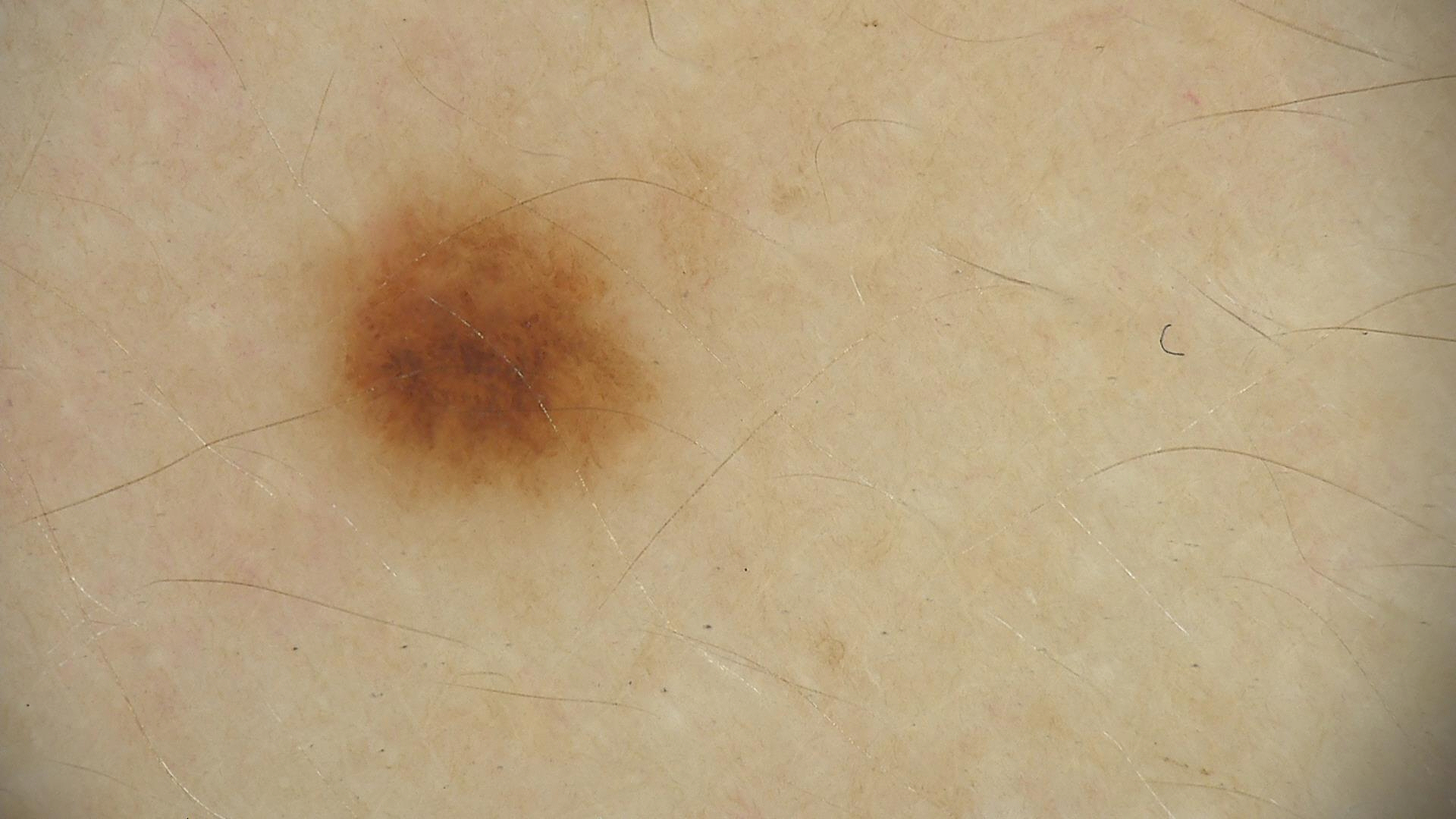image type: dermoscopy | assessment: dysplastic junctional nevus (expert consensus).